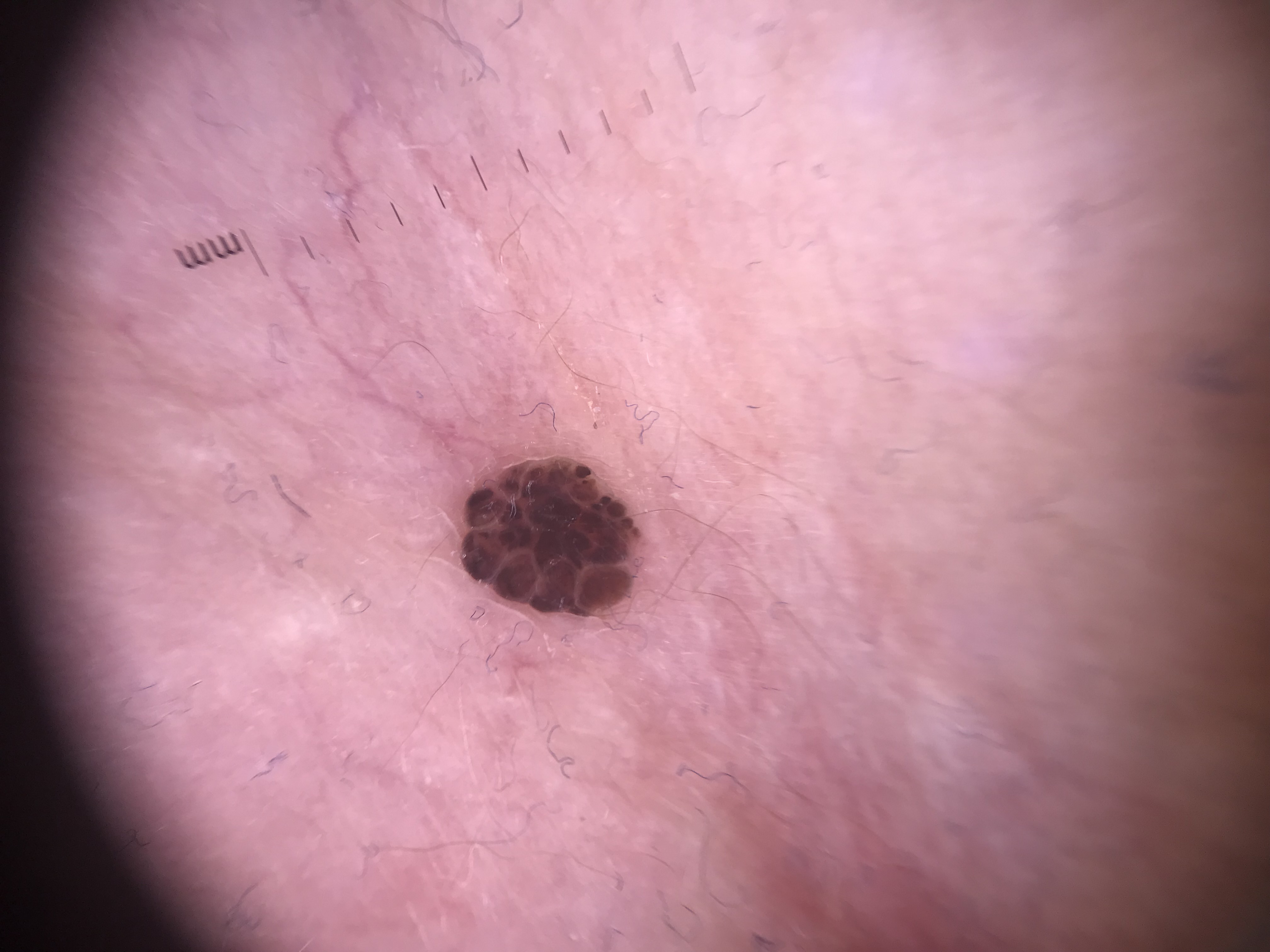Dermoscopy of a skin lesion. The diagnosis was a banal lesion — a compound nevus.